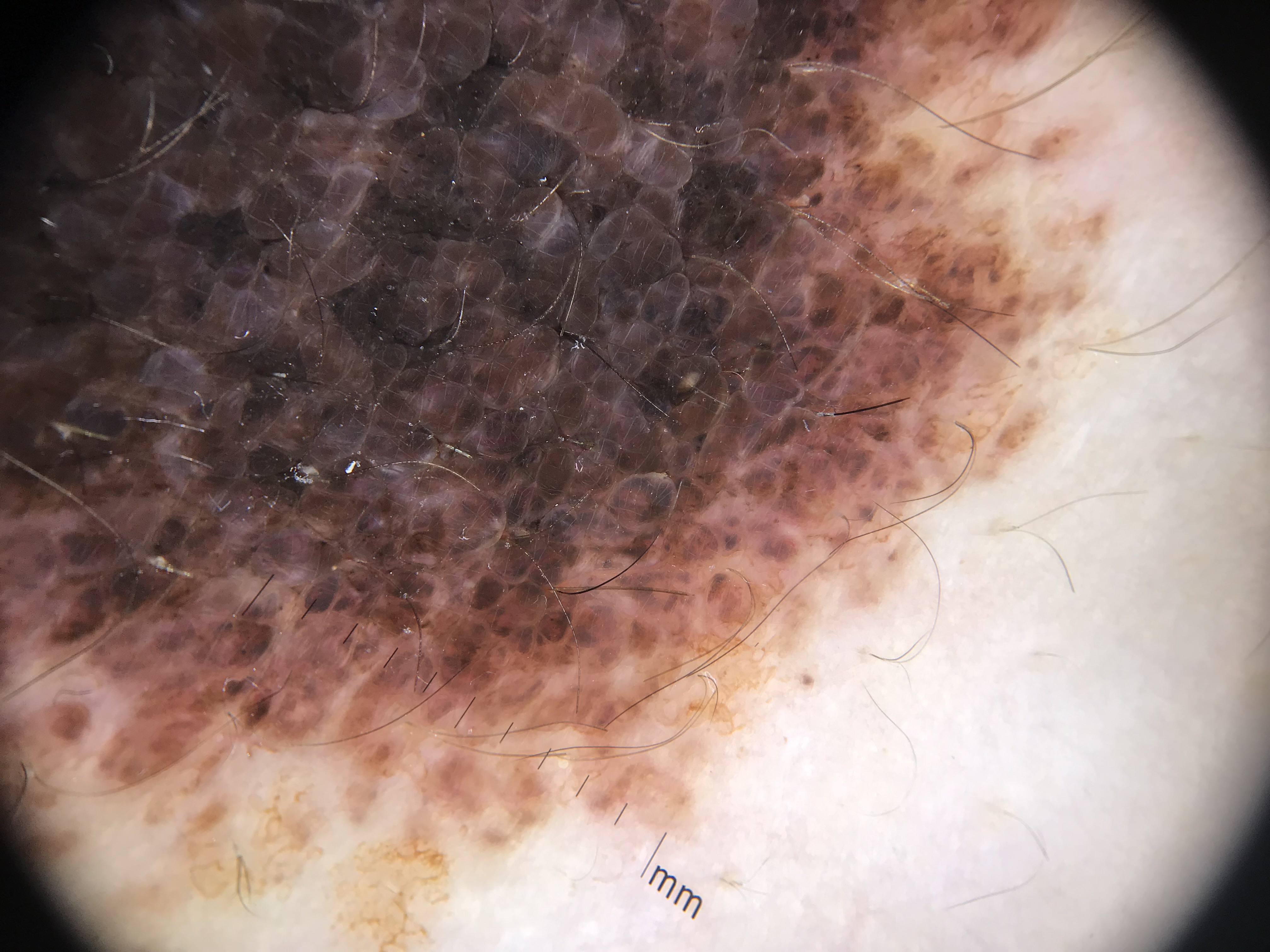Dermoscopy of a skin lesion. This is a banal lesion. Consistent with a congenital compound nevus.